A female subject roughly 60 years of age · the patient is FST II · a dermoscopic photograph of a skin lesion:
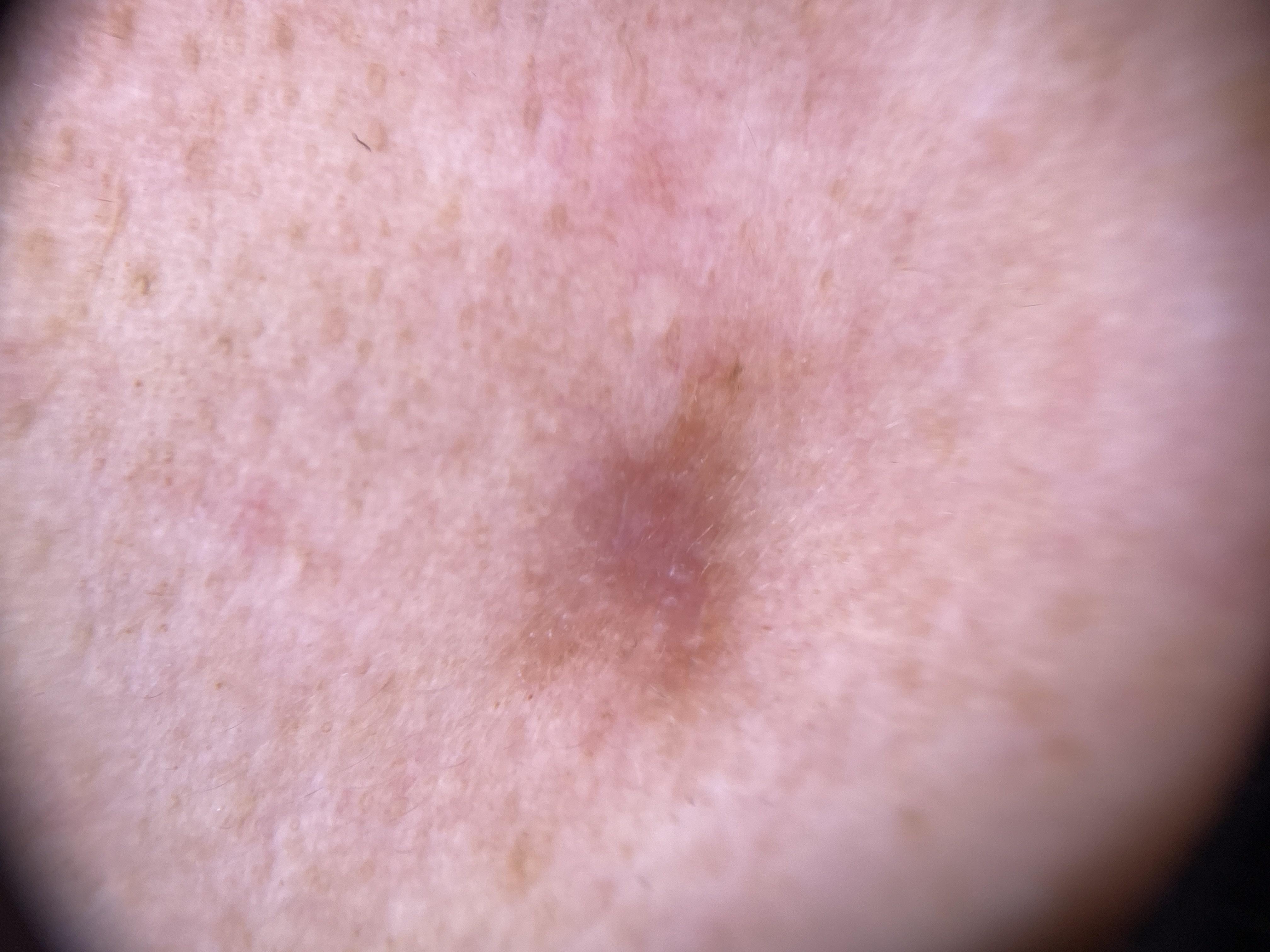– site — the head or neck
– pathology — Basal cell carcinoma (biopsy-proven)